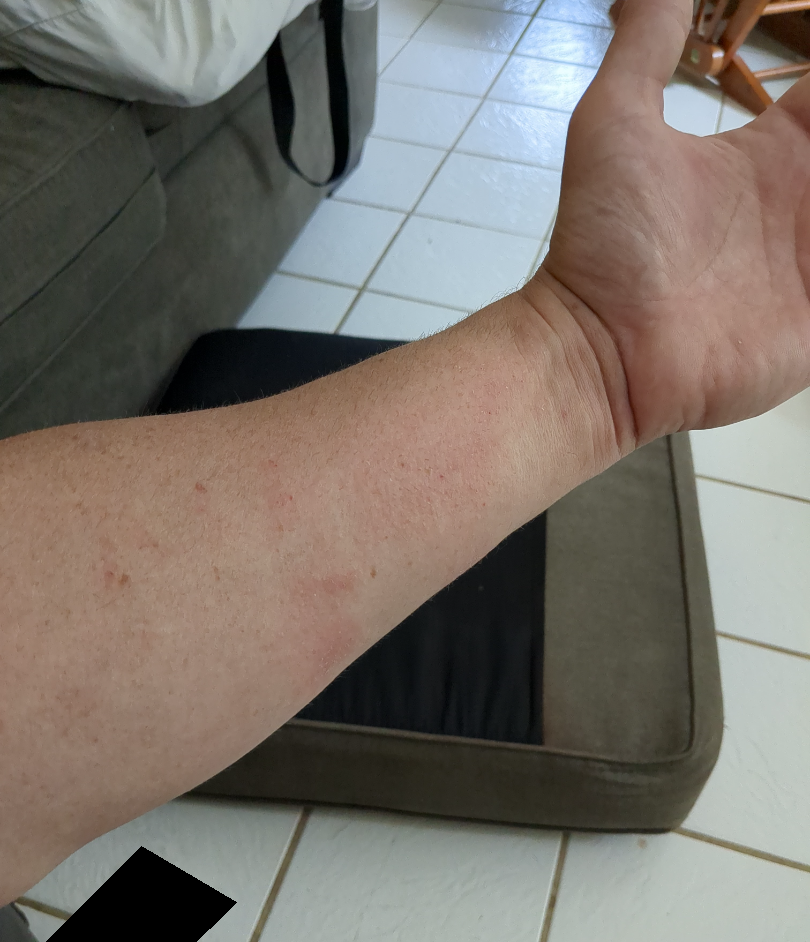On photographic review, most consistent with Eczema; possibly Irritant Contact Dermatitis; less probable is Allergic Contact Dermatitis.